This is a dermoscopic photograph of a skin lesion — 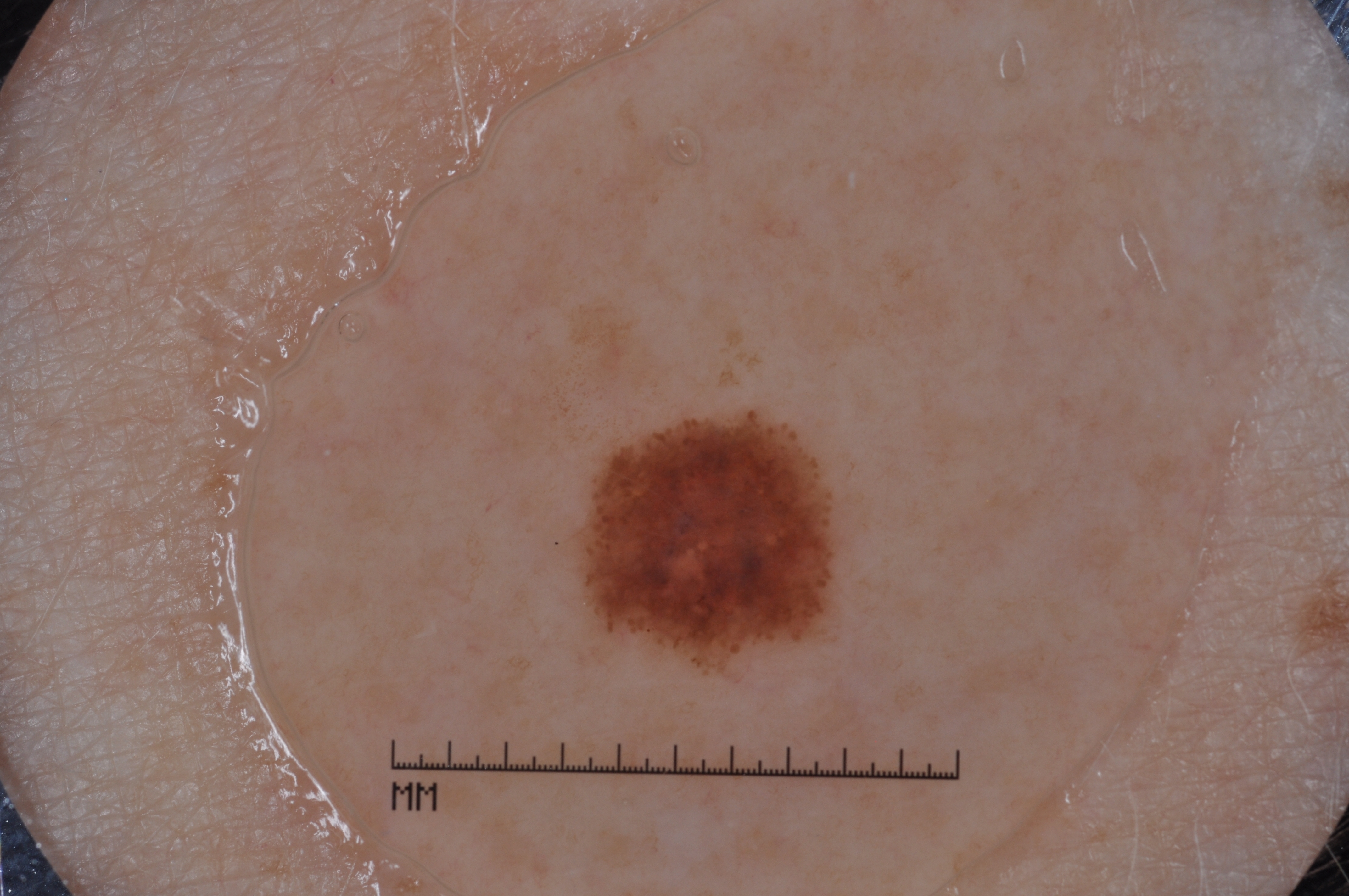The lesion takes up about 5% of the image. Dermoscopy demonstrates no milia-like cysts, streaks, negative network, or pigment network. The lesion is bounded by <box>553, 405, 856, 684</box>. Expert review diagnosed this as a melanocytic nevus, a benign lesion.